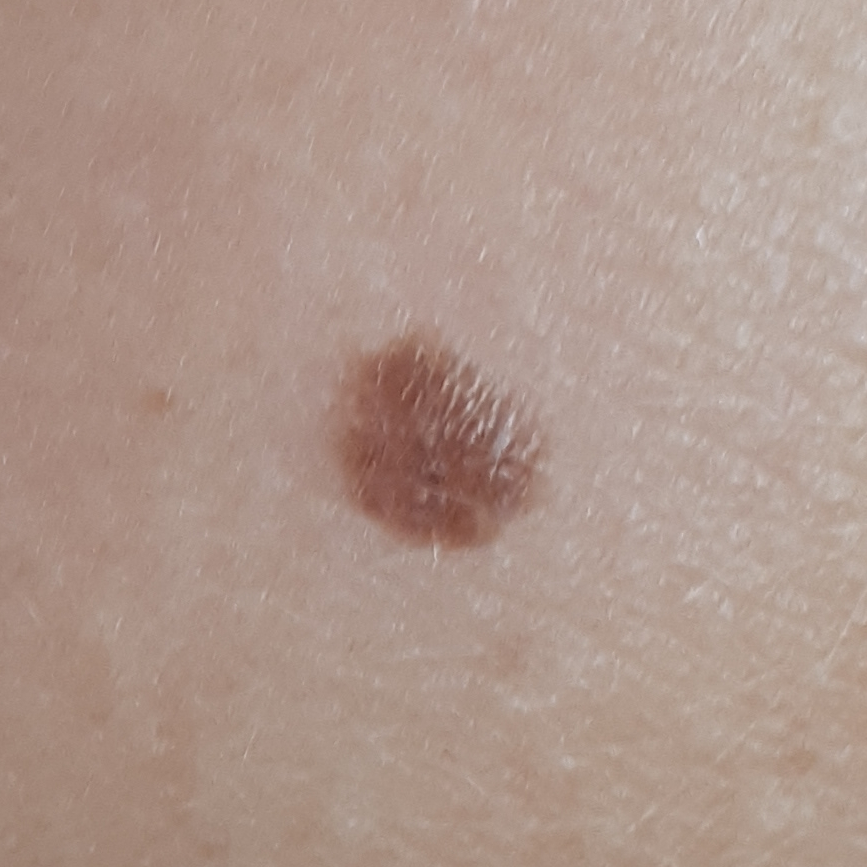A clinical photo of a skin lesion taken with a smartphone.
A patient 8 years of age.
The lesion involves the back.
Expert review favored a benign lesion — a nevus.